The patient is 50–59, female · located on the leg · the photo was captured at a distance.
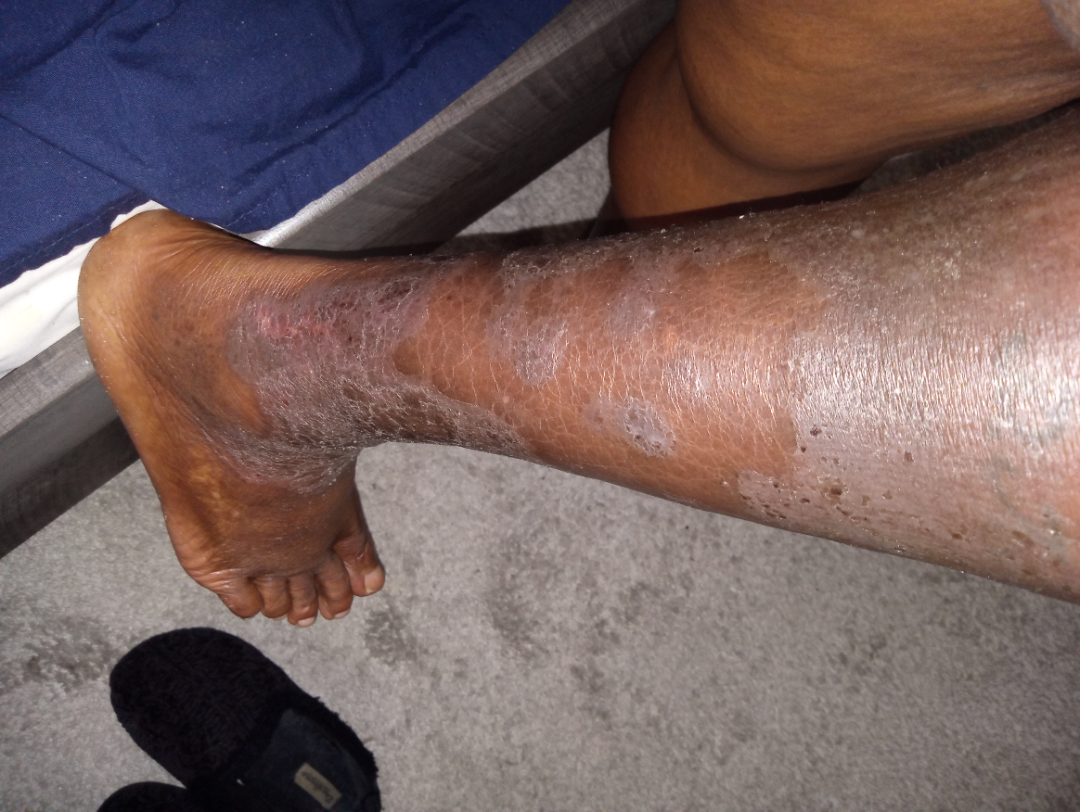symptoms = enlargement, itching, pain, burning, bothersome appearance and darkening
systemic symptoms = joint pain and fatigue
symptom duration = three to twelve months
lesion texture = fluid-filled and rough or flaky
assessment = one reviewing dermatologist: the primary impression is Infected eczema; also on the differential is Stasis Dermatitis